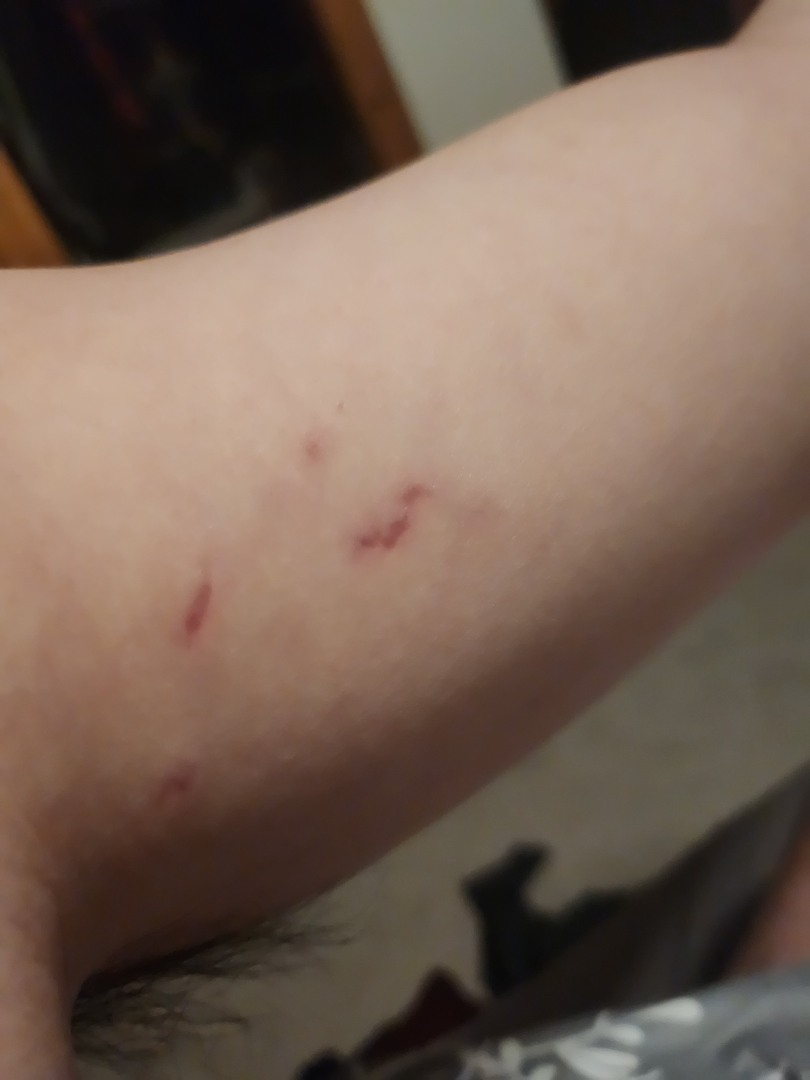Findings:
- history — one to three months
- surface texture — flat
- reported symptoms — enlargement and bothersome appearance
- associated systemic symptoms — none reported
- shot type — close-up
- anatomic site — arm
- differential diagnosis — Abrasion, scrape, or scab (weight 0.33); Skin striae (weight 0.33); Animal bite - wound (weight 0.33)